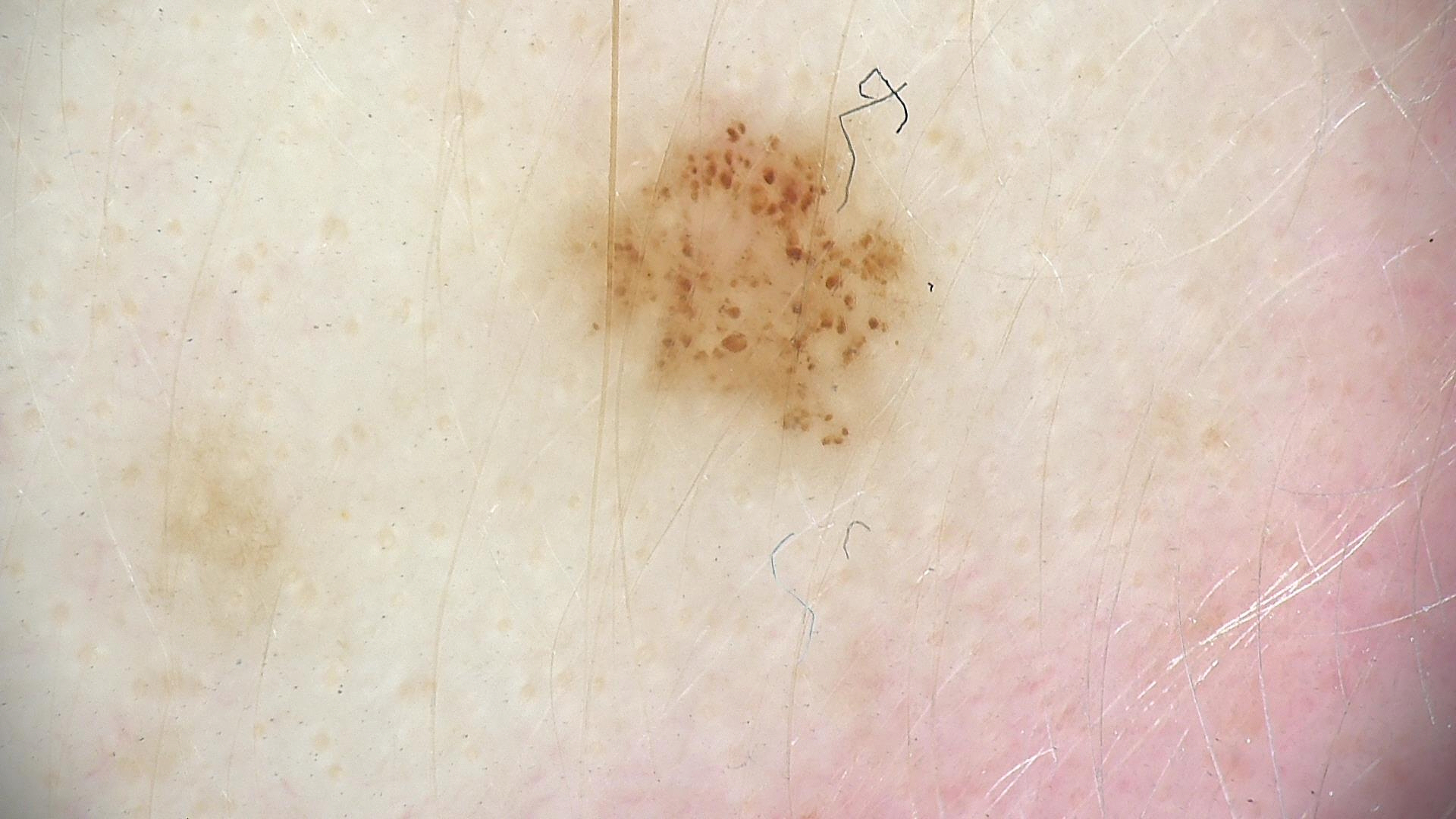modality — dermatoscopy | class — dysplastic junctional nevus (expert consensus).